A skin lesion imaged with contact-polarized dermoscopy; a female patient aged around 70:
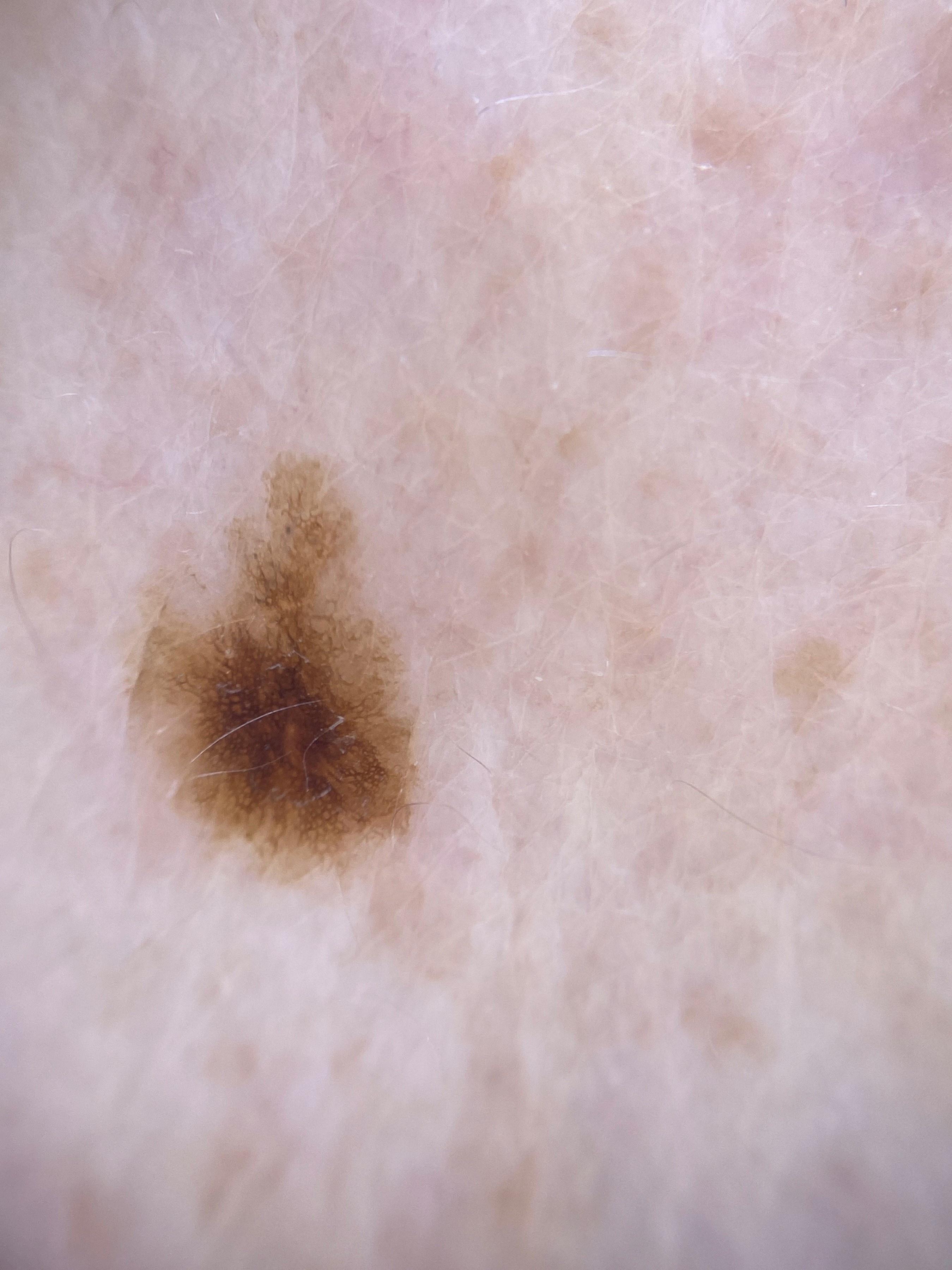diagnostic label: Nevus (clinical impression).